Dermoscopy of a skin lesion.
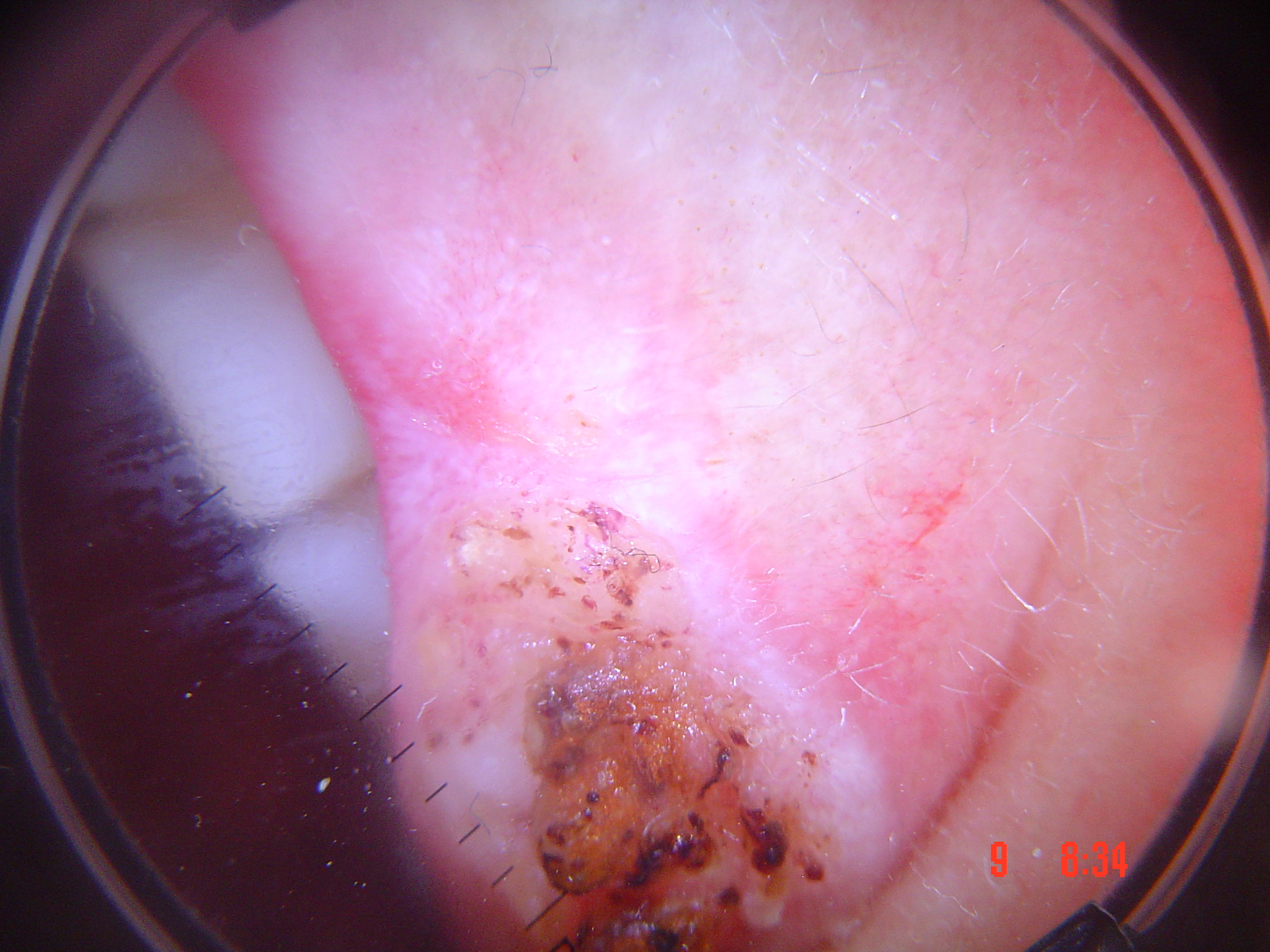<case>
<lesion_type>
<main_class>keratinocytic</main_class>
</lesion_type>
<diagnosis>
<name>squamous cell carcinoma</name>
<code>scc</code>
<malignancy>malignant</malignancy>
<super_class>non-melanocytic</super_class>
<confirmation>histopathology</confirmation>
</diagnosis>
</case>